Close-up view · the subject is male · the front of the torso is involved — 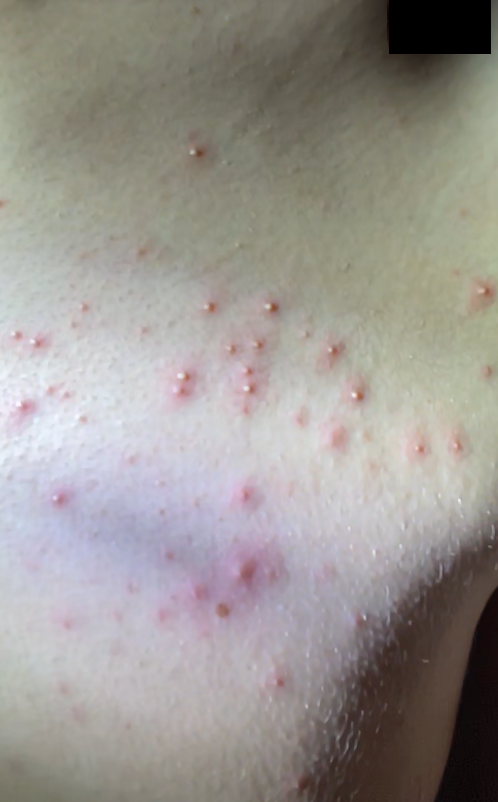differential diagnosis: most consistent with Folliculitis.